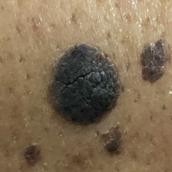A subject in their 50s.
The lesion is on the back.
The patient describes that the lesion is elevated, but has not grown and has not changed.
Diagnosed by dermatologist consensus as a seborrheic keratosis.